A dermoscopic image of a skin lesion; a female subject roughly 30 years of age; recorded as Fitzpatrick III — 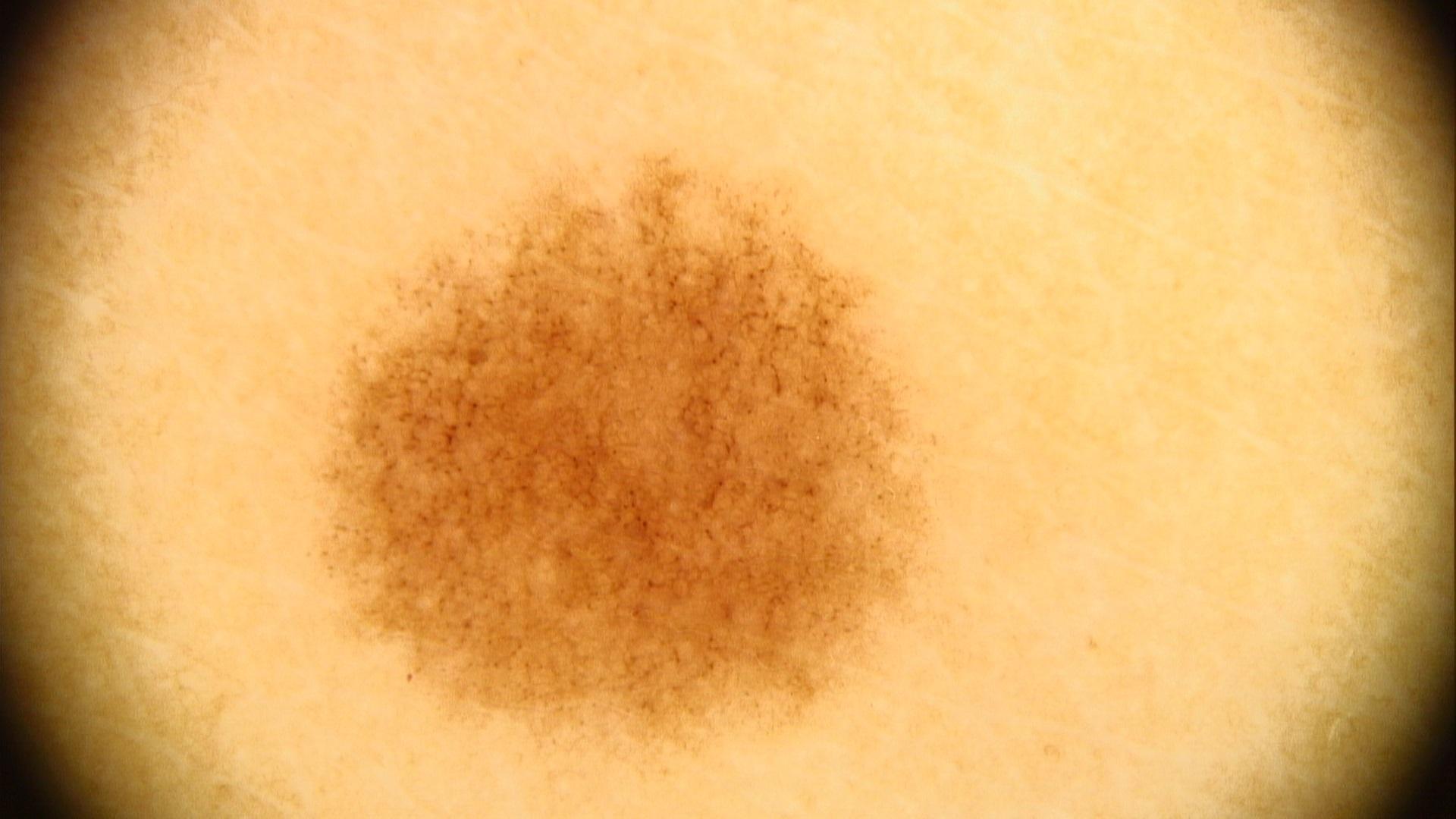site — a lower extremity | diagnostic label — Nevus (clinical impression).